Close-up view. The subject is a female aged 18–29. Located on the leg:
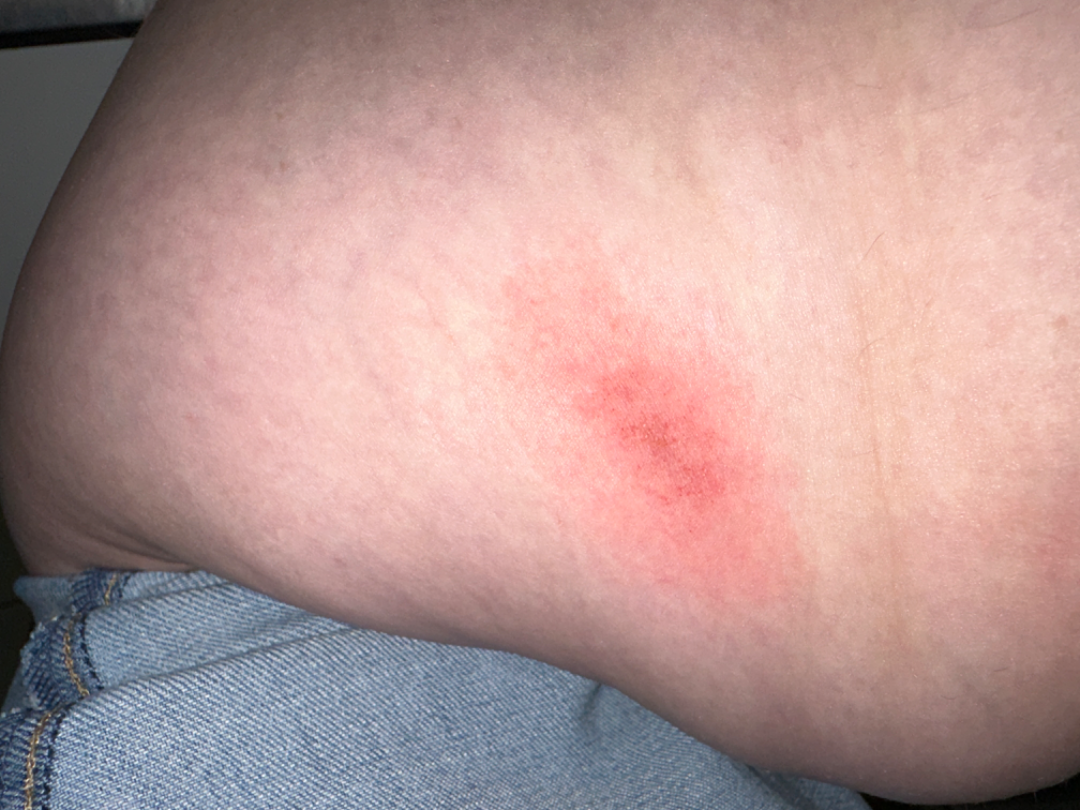The patient notes the condition has been present for about one day. Reported lesion symptoms include itching, pain and burning. On remote review of the image, Eczema (67%); Geographic tongue (33%).